Dermoscopy of a skin lesion.
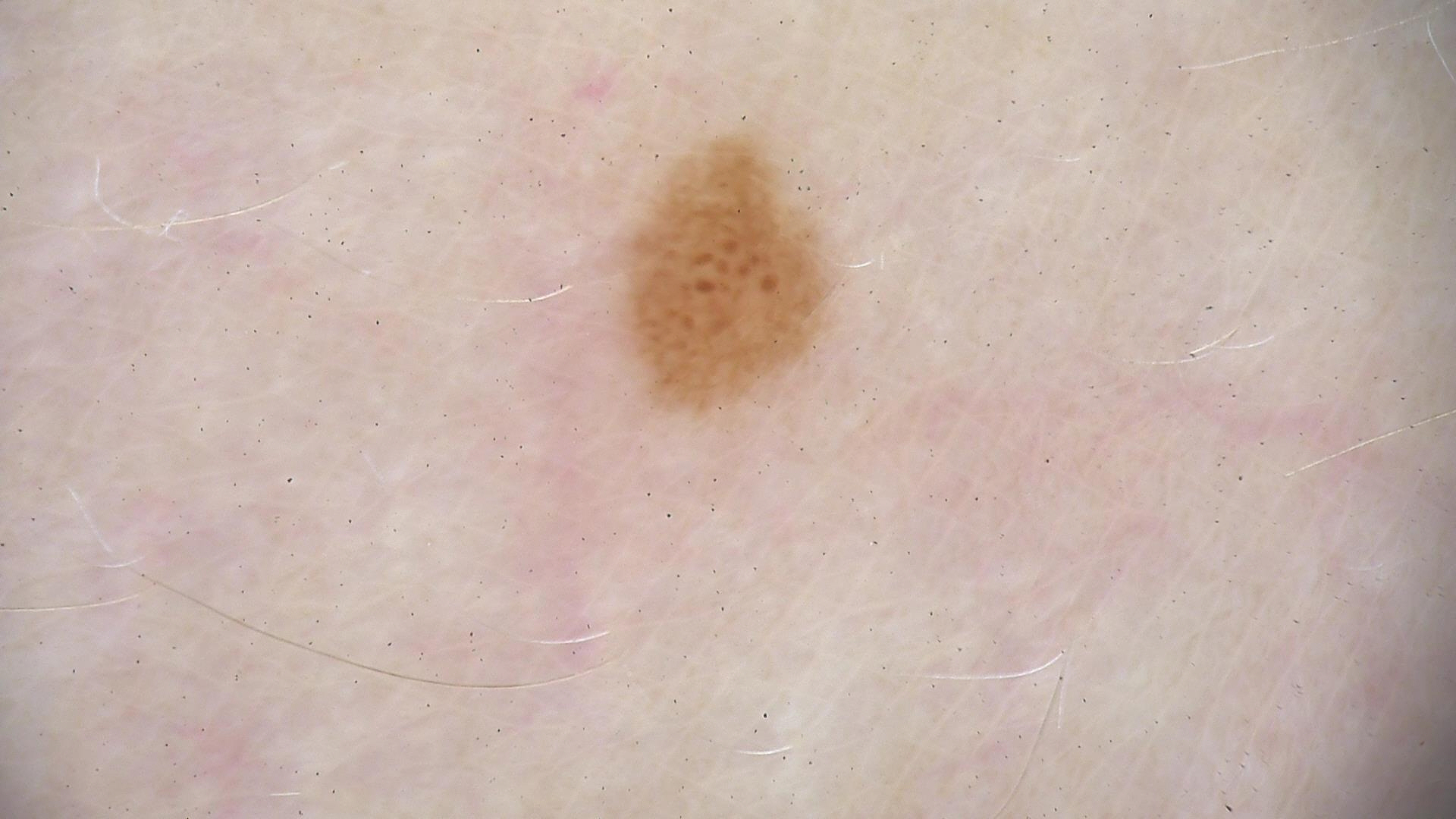Classified as a benign lesion — a dysplastic junctional nevus.